The patient is a male approximately 20 years of age, a dermatoscopic image of a skin lesion: 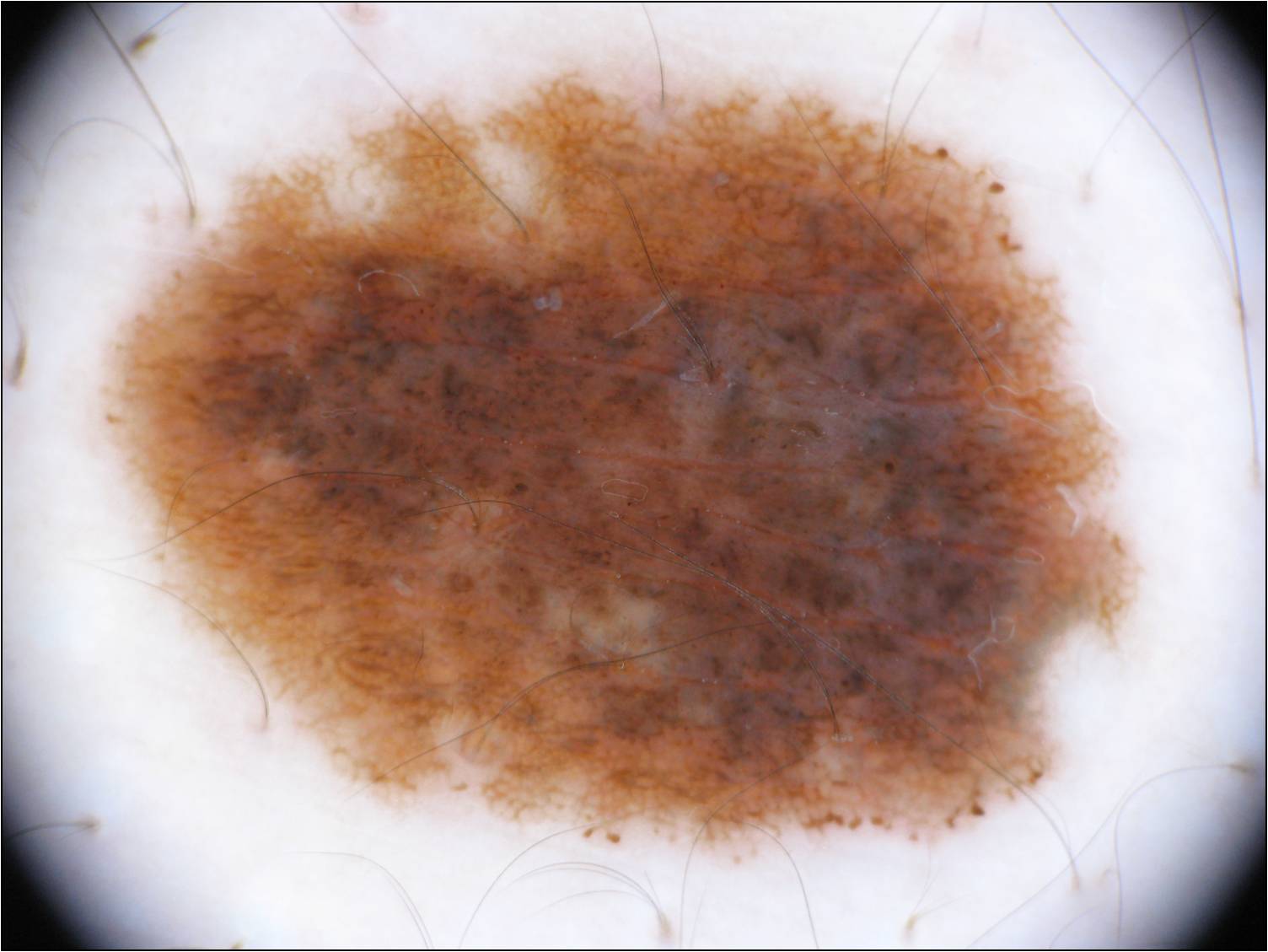The lesion occupies the region left=100, top=66, right=1133, bottom=847.
A large lesion occupying much of the field.
Dermoscopic review identifies pigment network and globules; no milia-like cysts, streaks, or negative network.
Consistent with a melanocytic nevus, a benign lesion.